A dermoscopic photograph of a skin lesion:
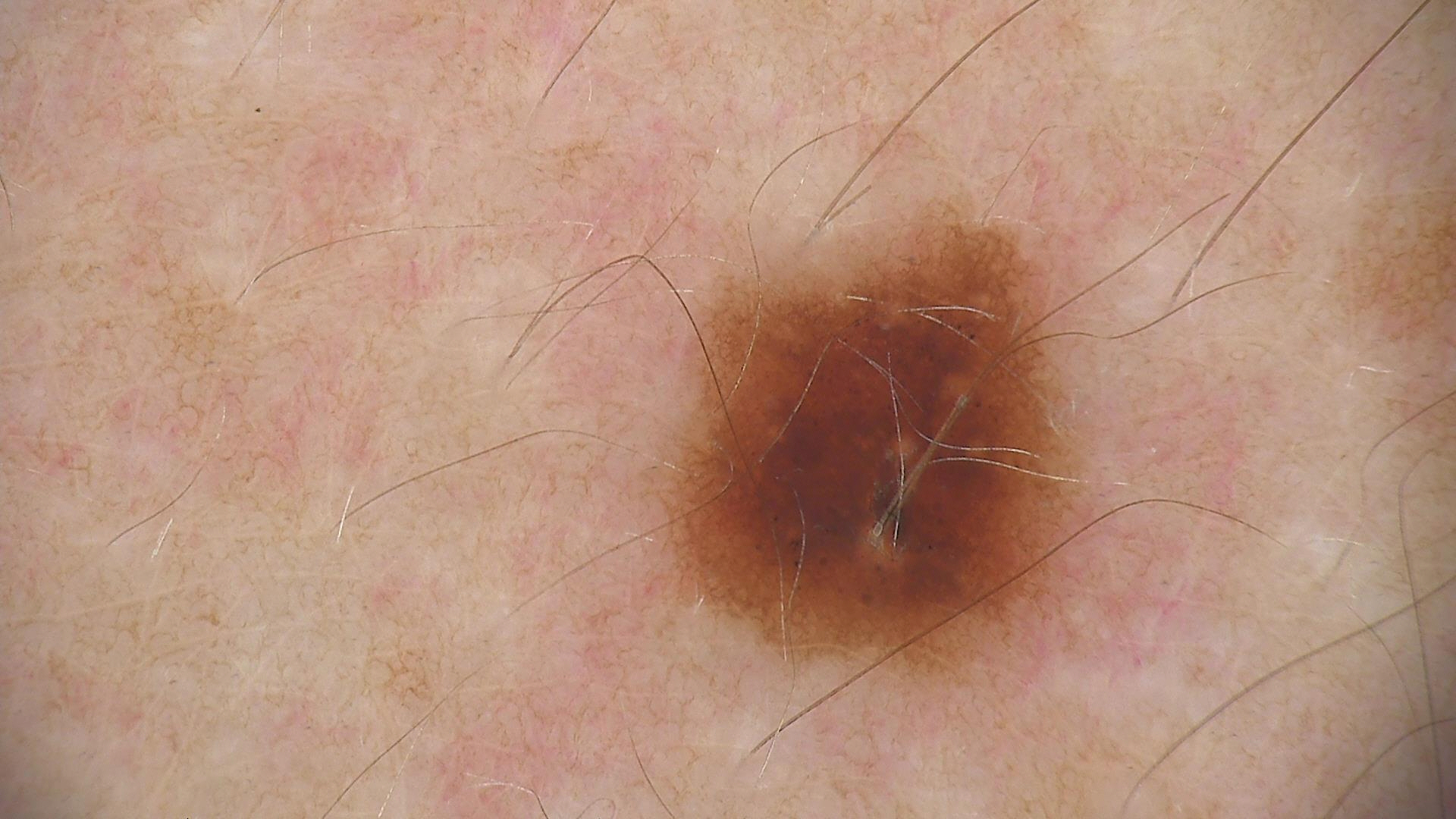Labeled as a benign lesion — a dysplastic junctional nevus.